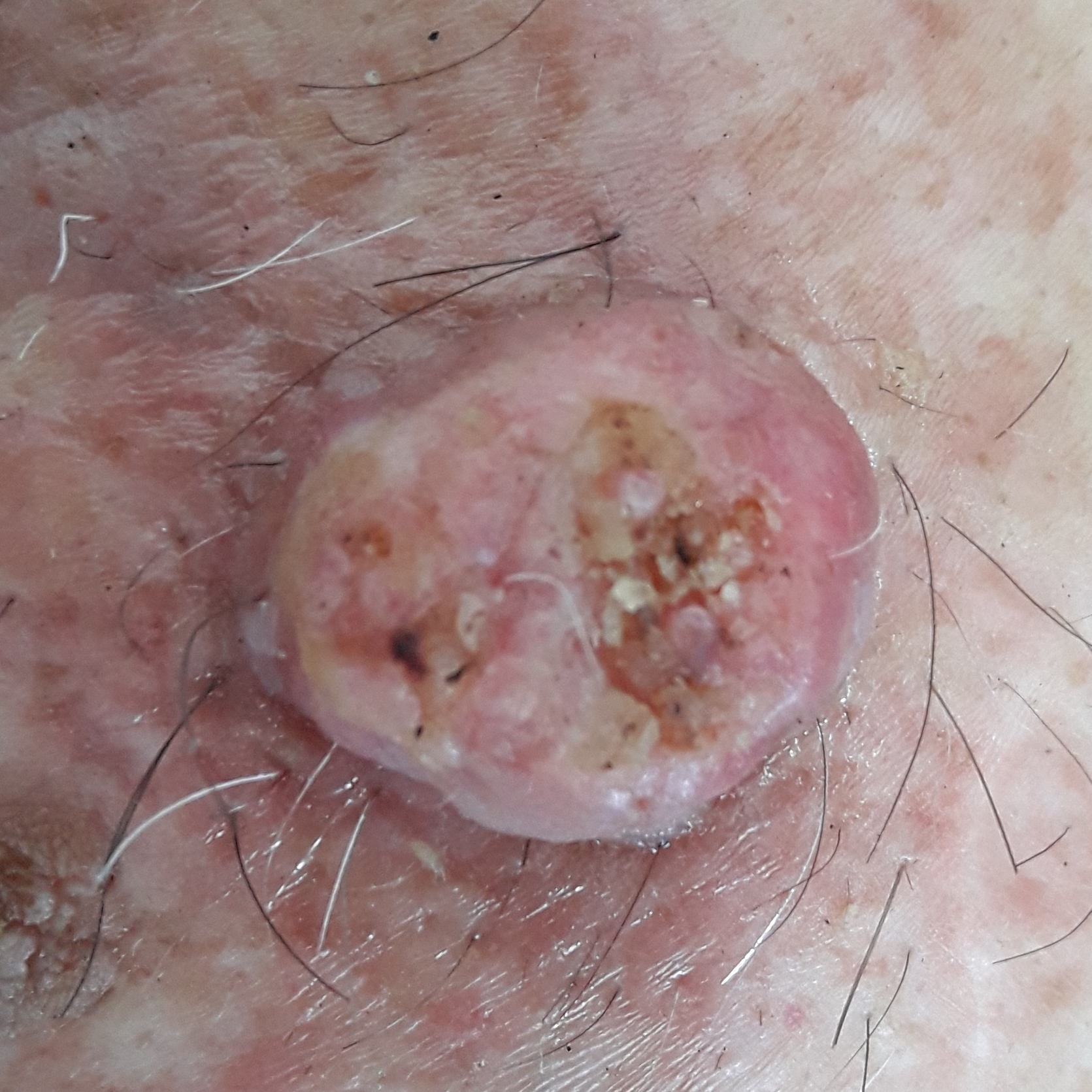skin type: II | modality: clinical photo | patient: male, 71 years of age | risk factors: prior skin cancer (patient or family), tobacco use, alcohol use, prior malignancy (patient or family), pesticide exposure | region: the chest | lesion size: approx. 8 × 7 mm | symptoms: elevation, itching, growth | diagnostic label: basal cell carcinoma (biopsy-proven).